A female subject in their late 50s: 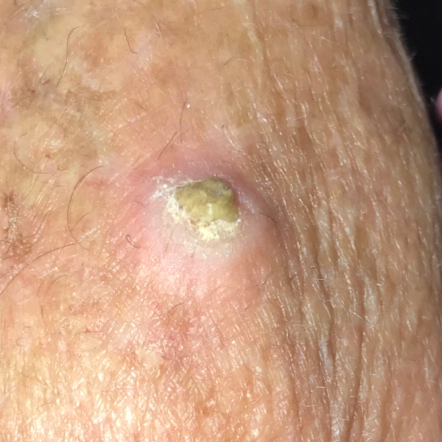Clinical context:
The lesion is located on a hand. The patient describes that the lesion itches and is elevated.
Pathology:
The biopsy diagnosis was an actinic keratosis.